A close-up photograph — 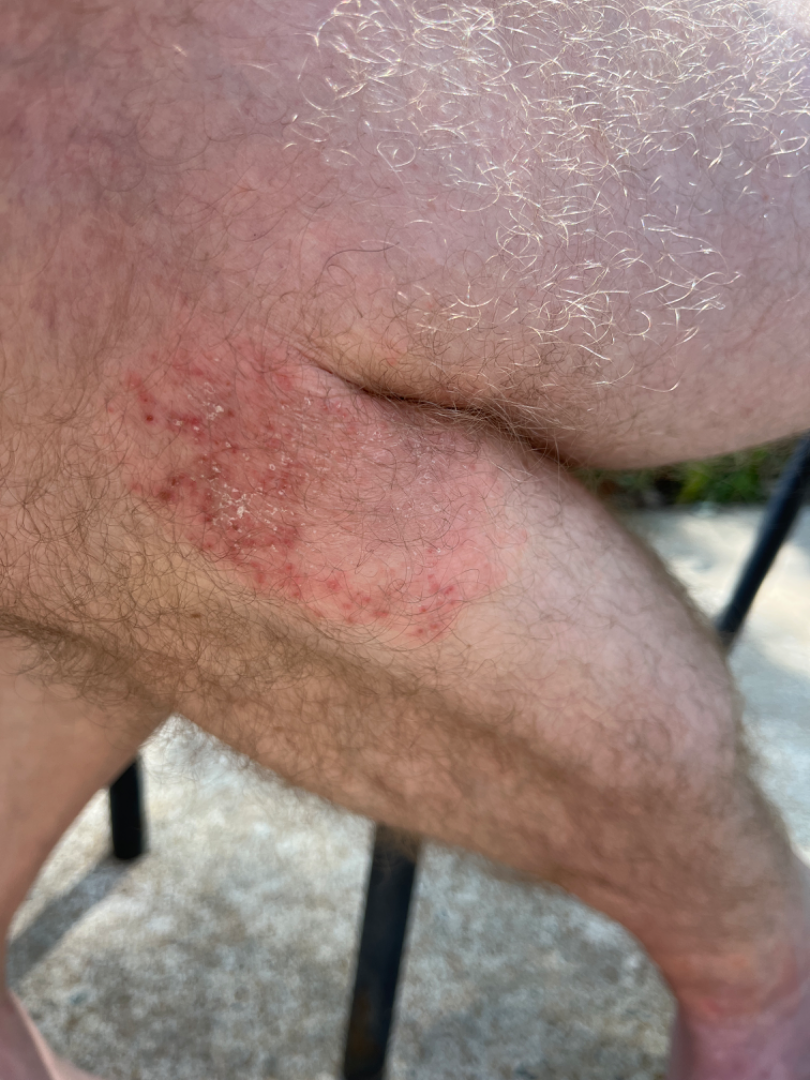On photographic review, Tinea and Acute and chronic dermatitis were each considered, in no particular order.